Female patient, age 40–49 · the arm, back of the hand and leg are involved · the photo was captured at a distance: 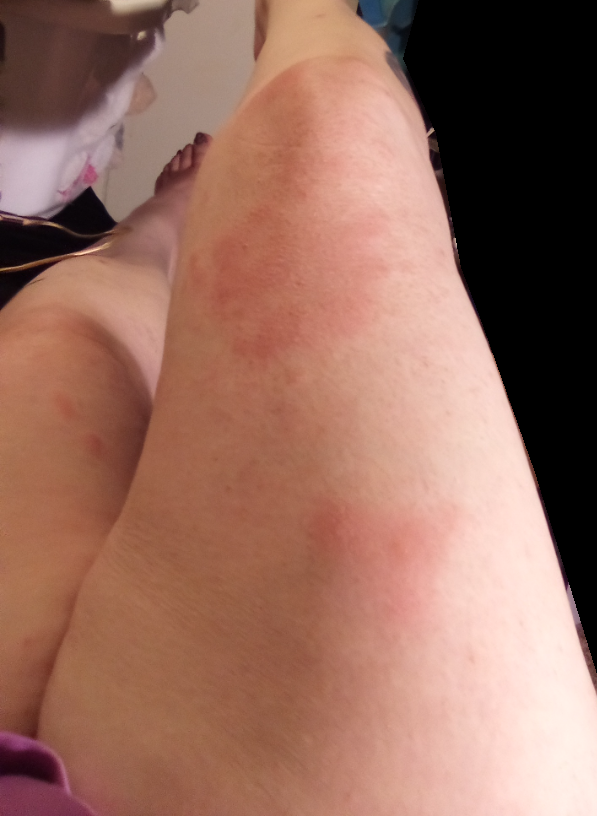{
  "differential": {
    "leading": [
      "Allergic Contact Dermatitis"
    ],
    "considered": [
      "Hypersensitivity"
    ]
  }
}